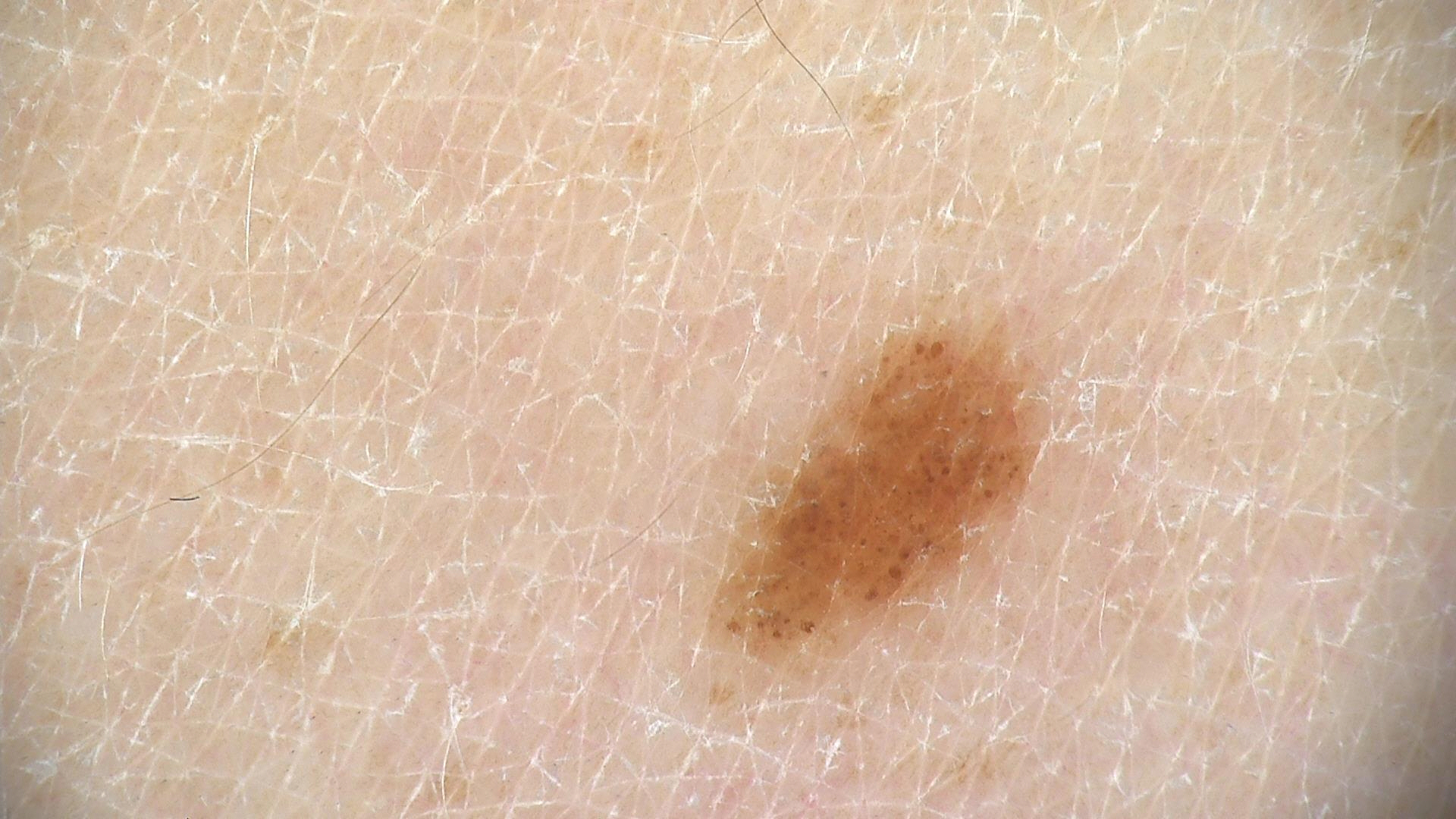A dermoscopic close-up of a skin lesion.
The architecture is that of a banal lesion.
Consistent with a junctional nevus.